A dermoscopic close-up of a skin lesion.
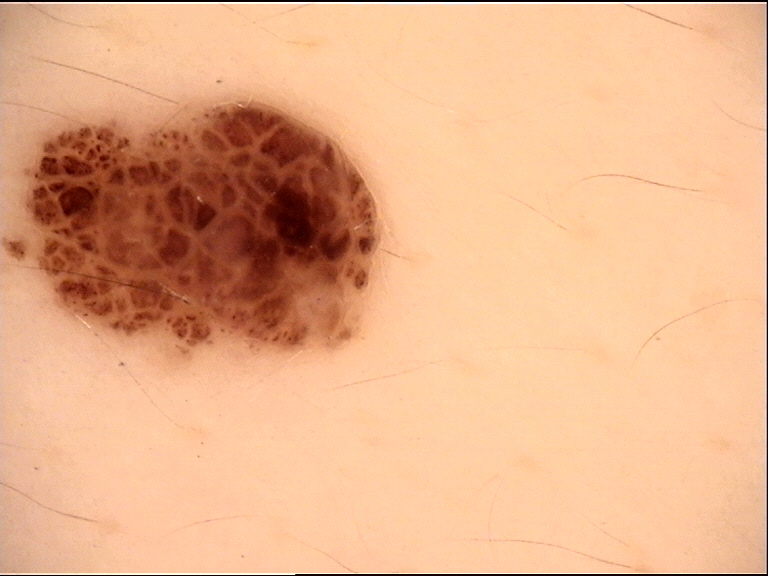diagnosis = compound nevus (expert consensus)